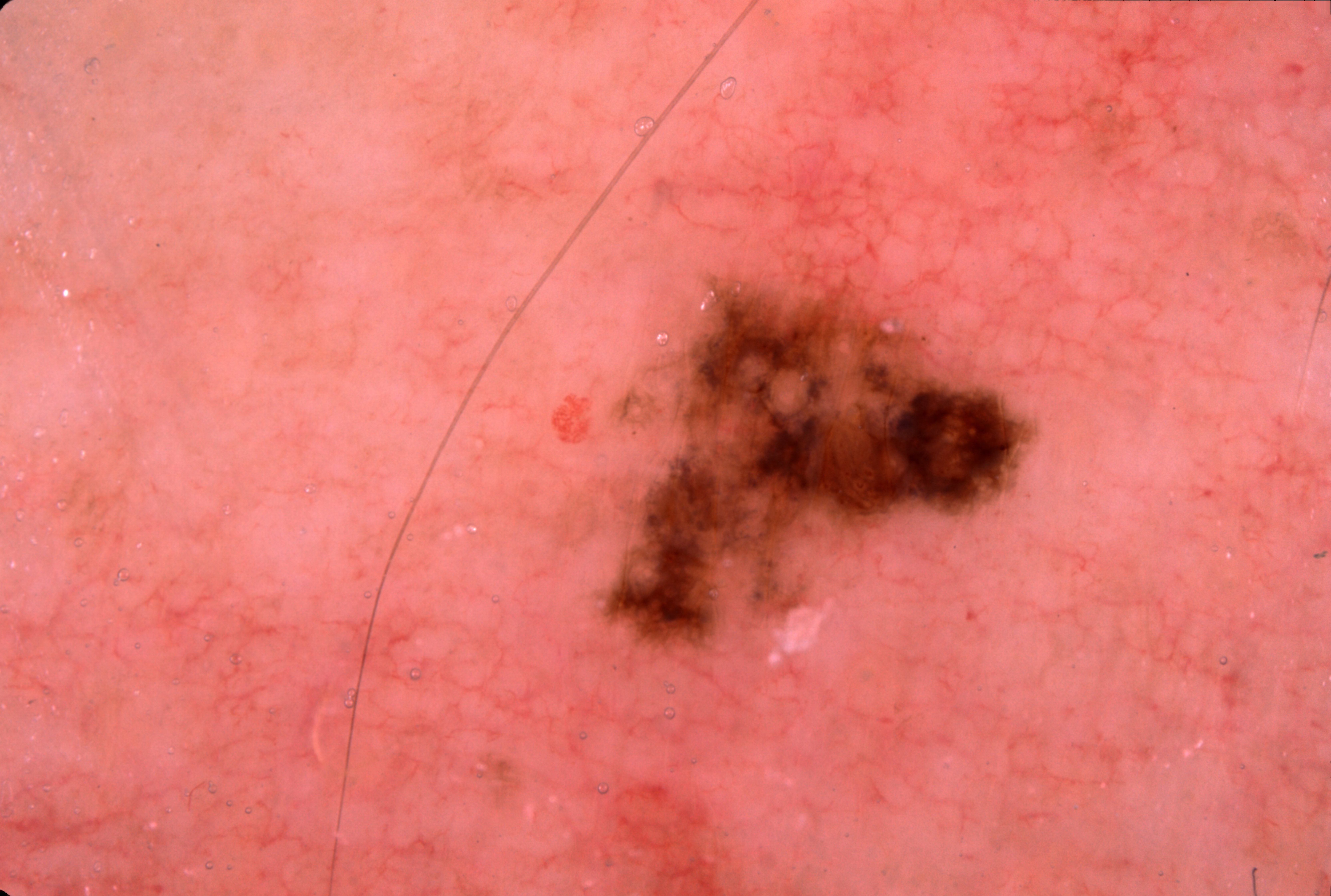{"patient": {"sex": "male", "age_approx": 60}, "image": {"modality": "dermoscopy"}, "dermoscopic_features": {"present": [], "absent": ["milia-like cysts", "streaks", "pigment network", "negative network"]}, "lesion_extent": "moderate", "lesion_location": {"bbox_xyxy": [586, 247, 1039, 684]}, "diagnosis": {"name": "melanocytic nevus", "malignancy": "benign", "lineage": "melanocytic", "provenance": "clinical"}}